Texture is reported as flat and raised or bumpy. The contributor is 18–29, female. The lesion involves the arm and back of the hand. The patient notes the condition has been present for more than one year. The lesion is associated with darkening, enlargement and bothersome appearance. Self-categorized by the patient as a pigmentary problem. A close-up photograph: 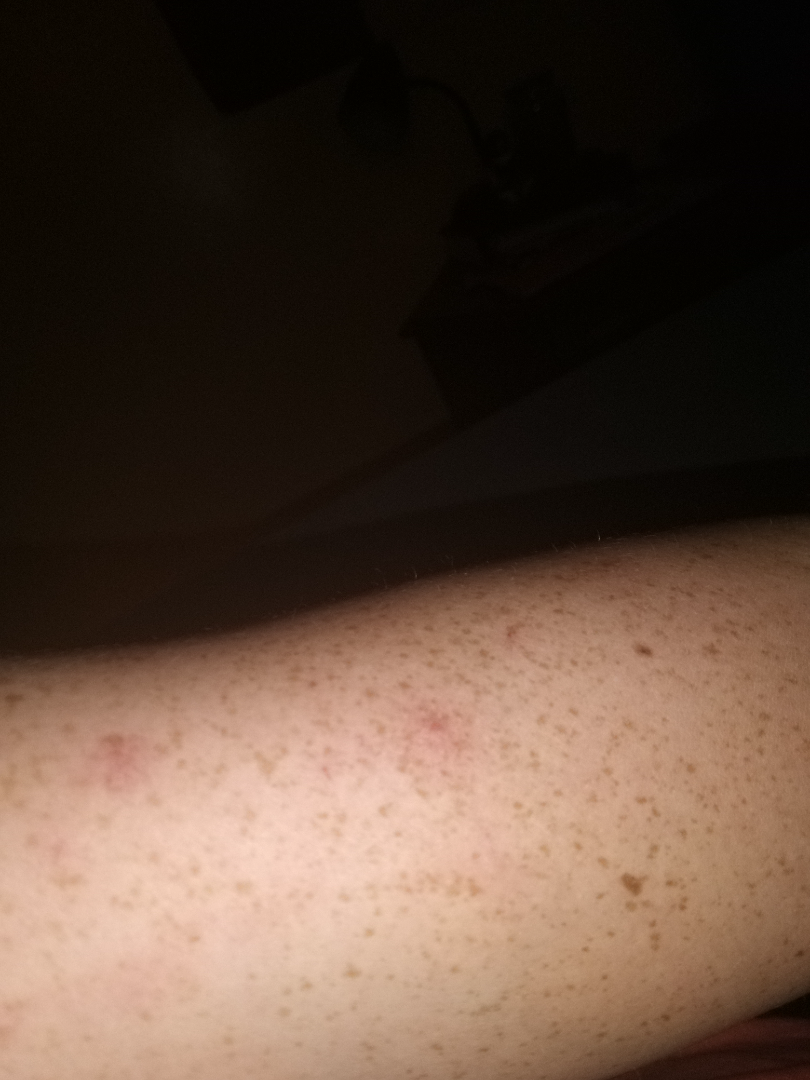Q: What is the dermatologist's impression?
A: the impression was split between Folliculitis and Insect Bite